Texture is reported as rough or flaky. Skin tone: Fitzpatrick skin type III; human graders estimated Monk Skin Tone 2 or 4. The contributor is 30–39, female. The affected area is the leg, arm and front of the torso. A close-up photograph. The patient indicates pain, itching and burning:
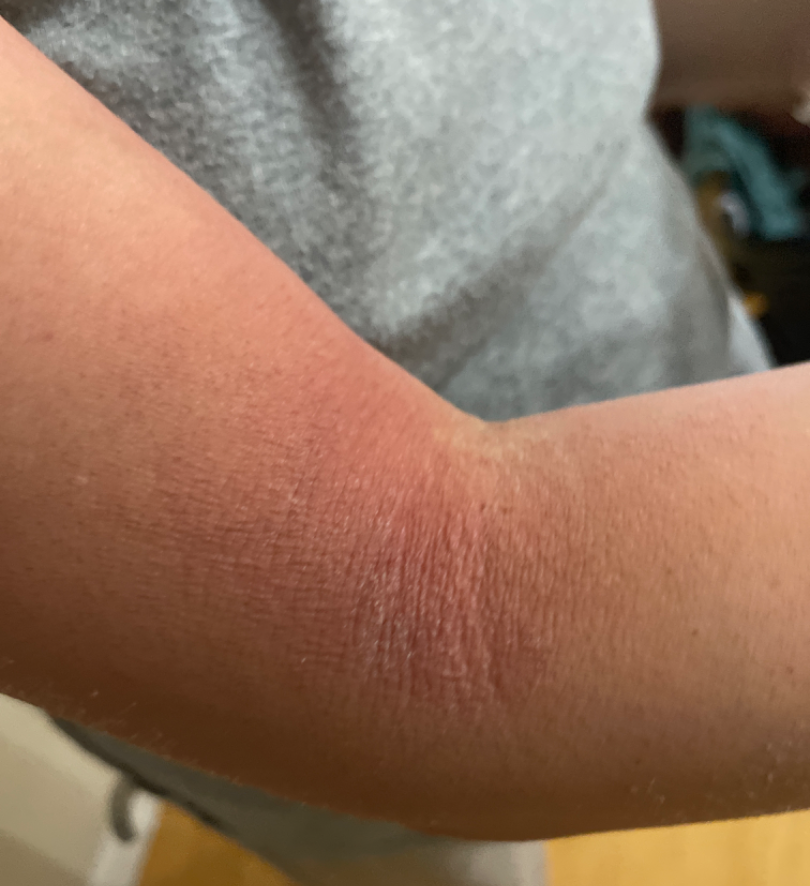Q: What conditions are considered?
A: most consistent with Eczema; possibly Xerosis; less probable is Lichen Simplex Chronicus